The contributor notes the lesion is flat, the patient is male, self-categorized by the patient as skin that appeared healthy to them, the contributor notes the condition has been present for three to twelve months, symptoms reported: darkening, an image taken at an angle, the affected area is the head or neck:
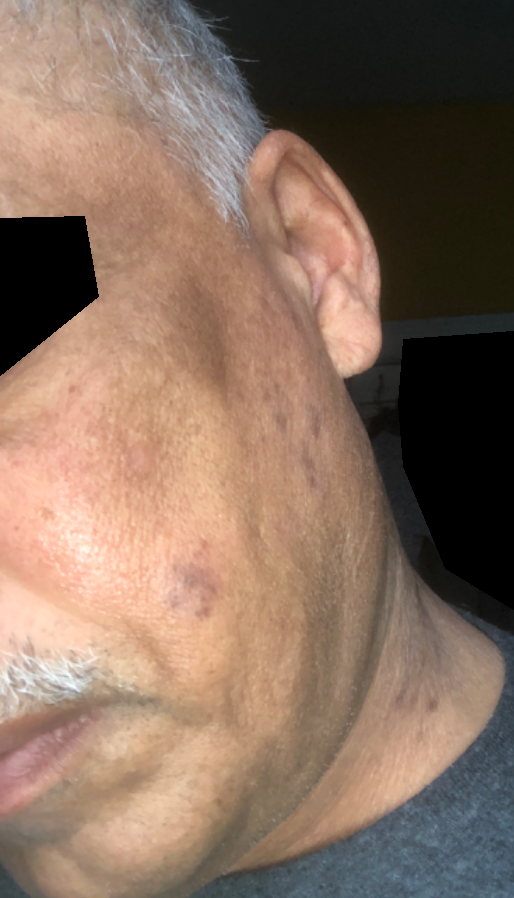Findings: Prurigo nodularis and Cutaneous lupus were each considered, in no particular order.